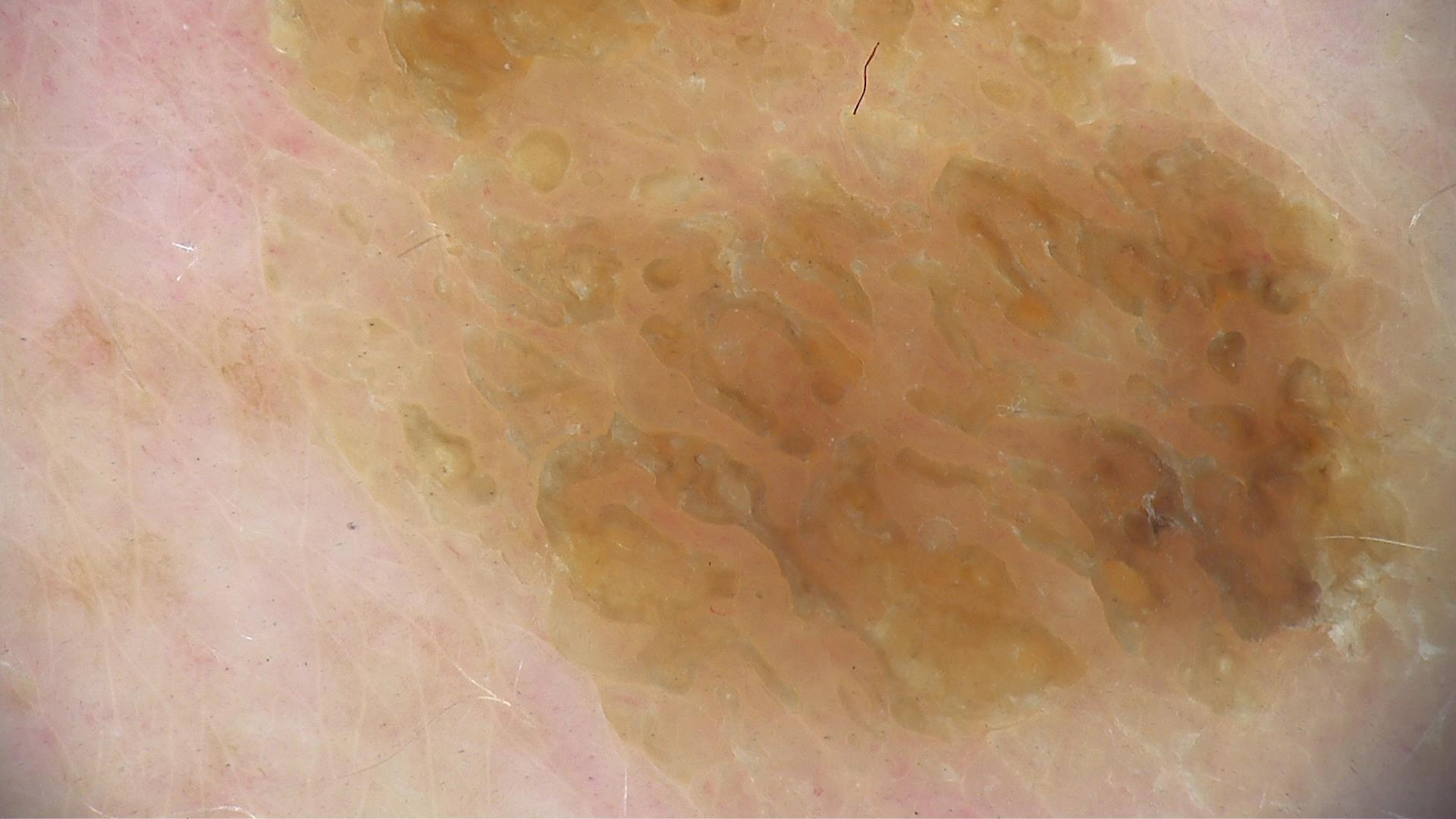Q: What is the diagnosis?
A: seborrheic keratosis (expert consensus)